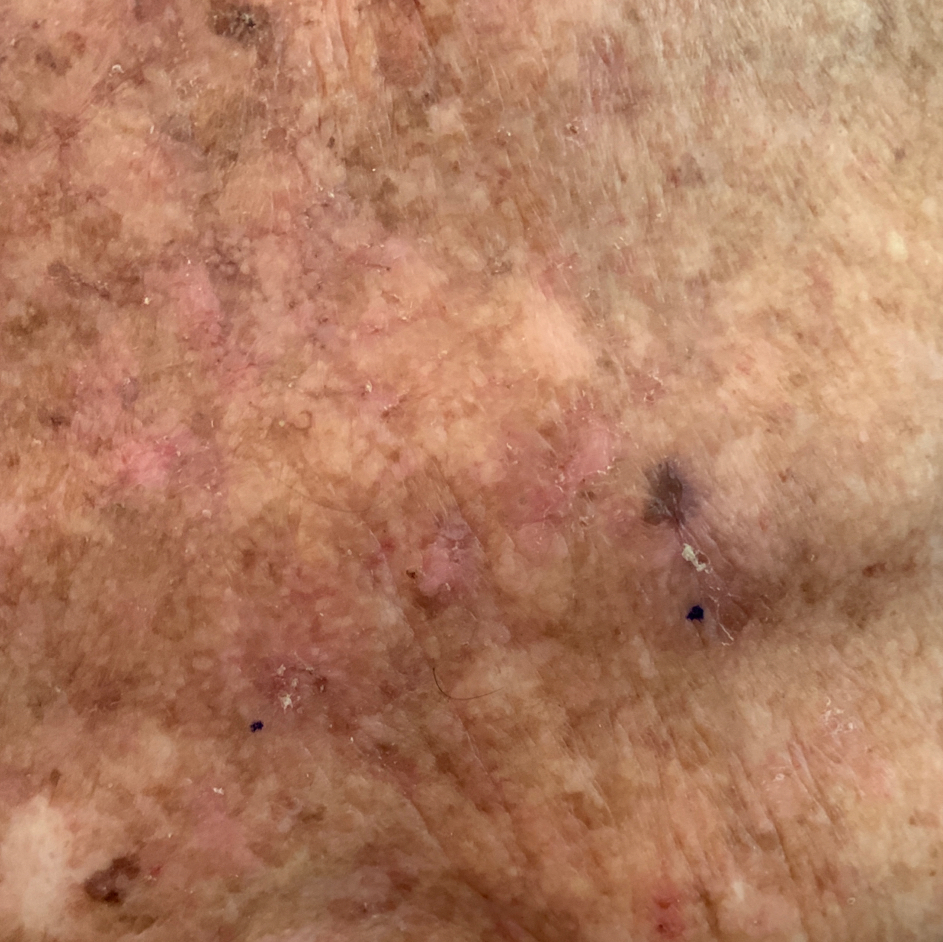| feature | finding |
|---|---|
| patient-reported symptoms | none reported |
| assessment | actinic keratosis (clinical consensus) |